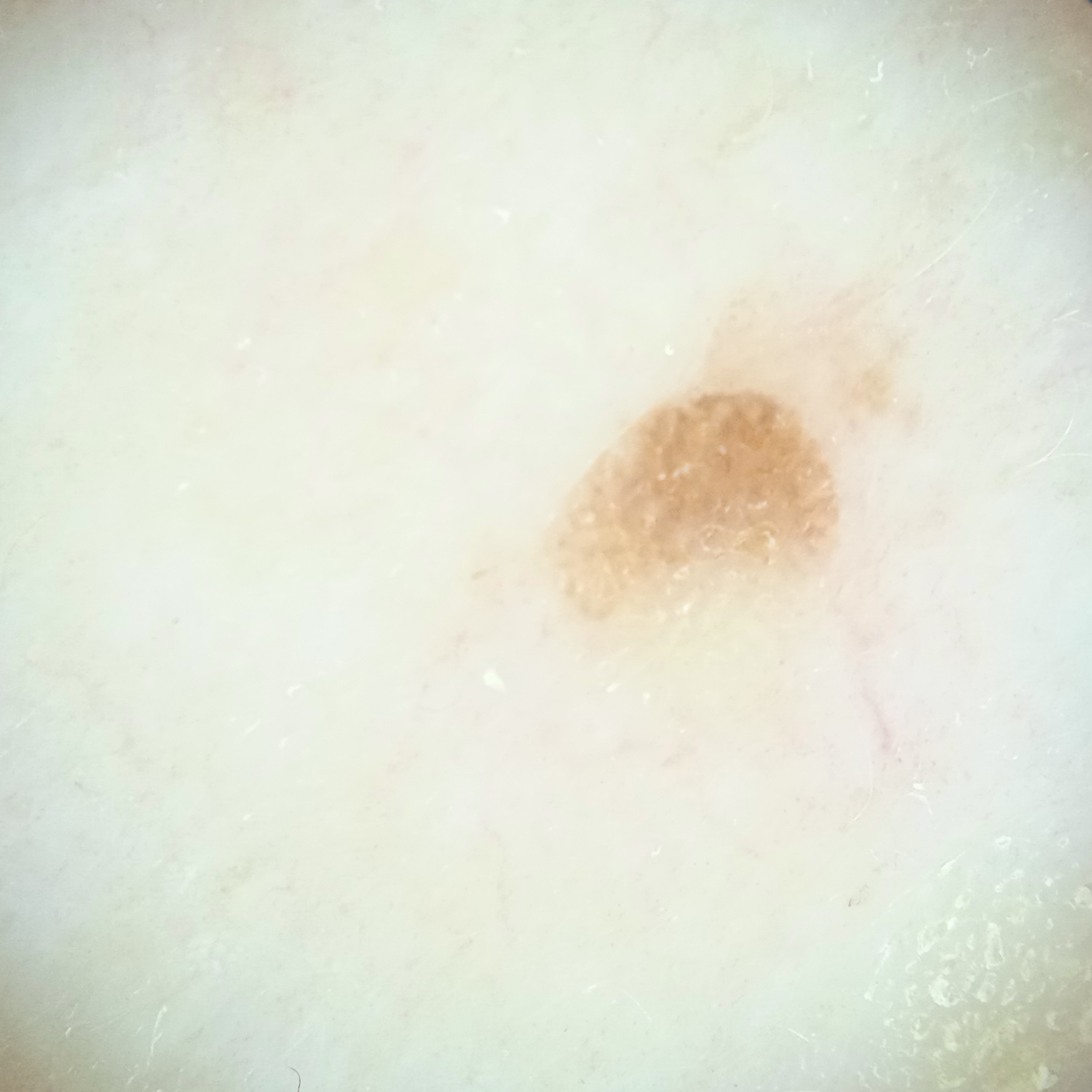Q: What kind of image is this?
A: dermoscopy
Q: What are the relevant risk factors?
A: a personal history of cancer, a personal history of skin cancer
Q: What was the diagnosis?
A: seborrheic keratosis (dermatologist consensus)